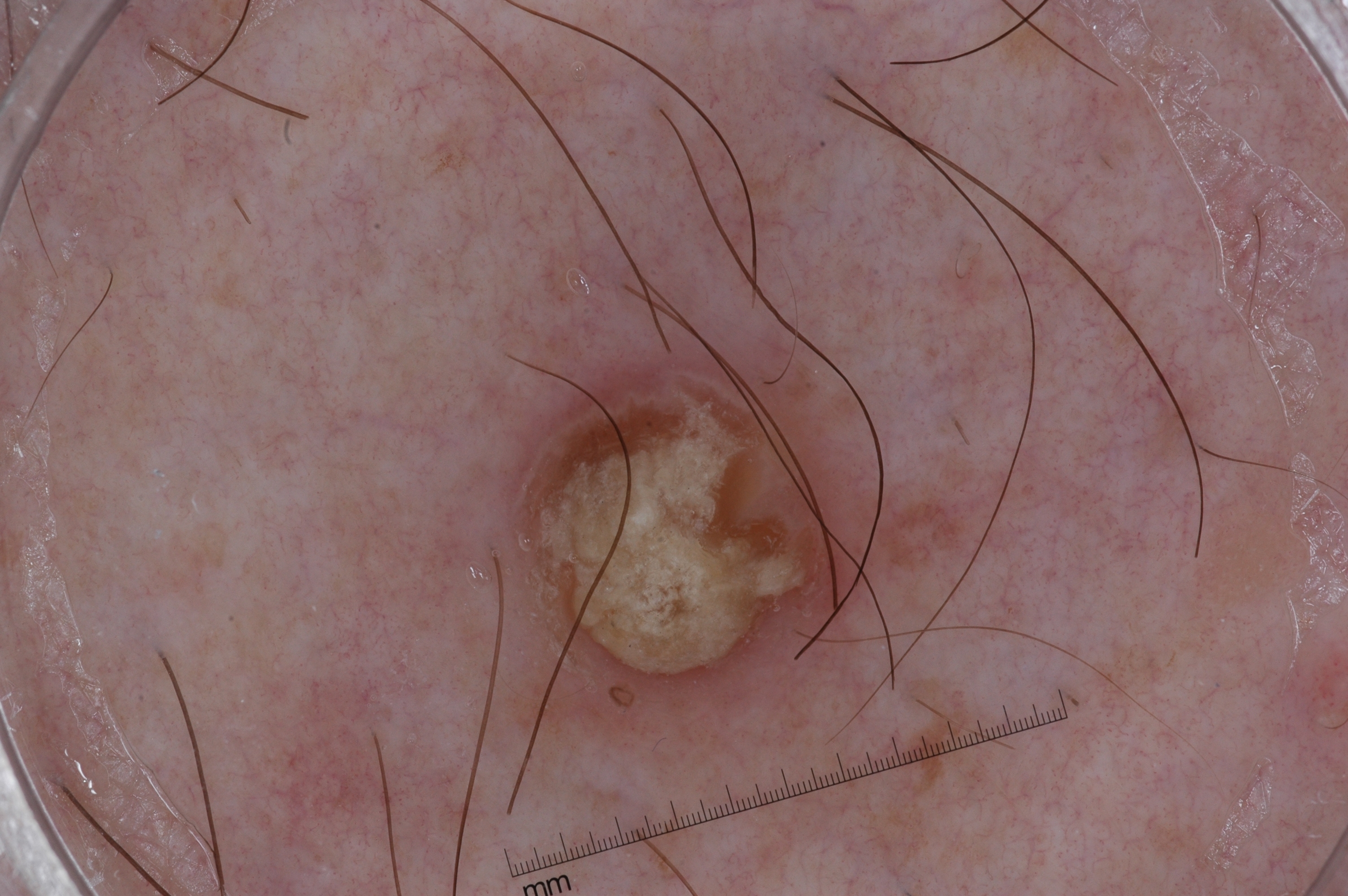patient = male, in their 70s; imaging = dermoscopy; lesion location = <bbox>390, 175, 1000, 763</bbox>; dermoscopic features not present = milia-like cysts, pigment network, streaks, and negative network; impression = a seborrheic keratosis.